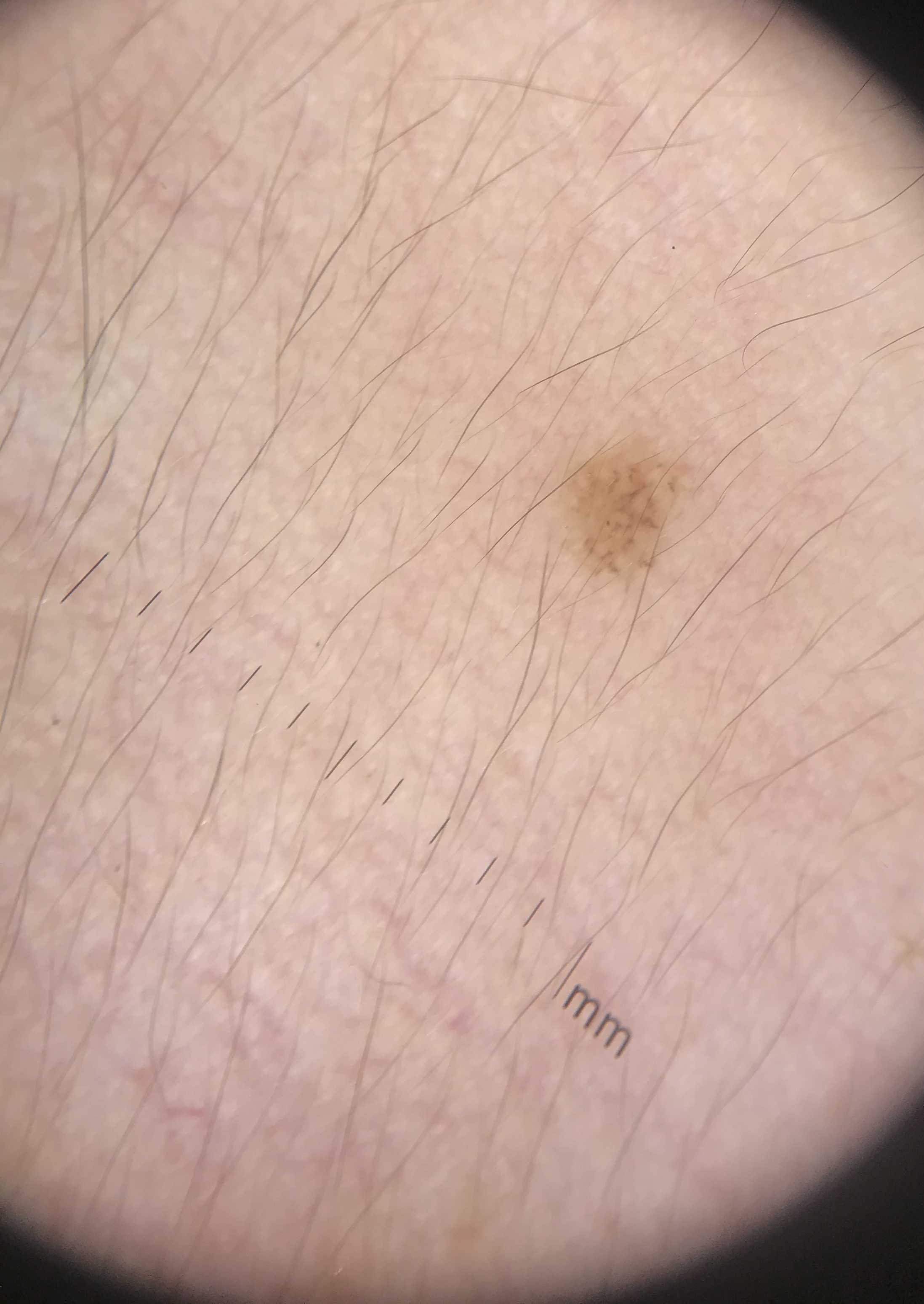The architecture is that of a compound, banal lesion.
Classified as a Miescher nevus.